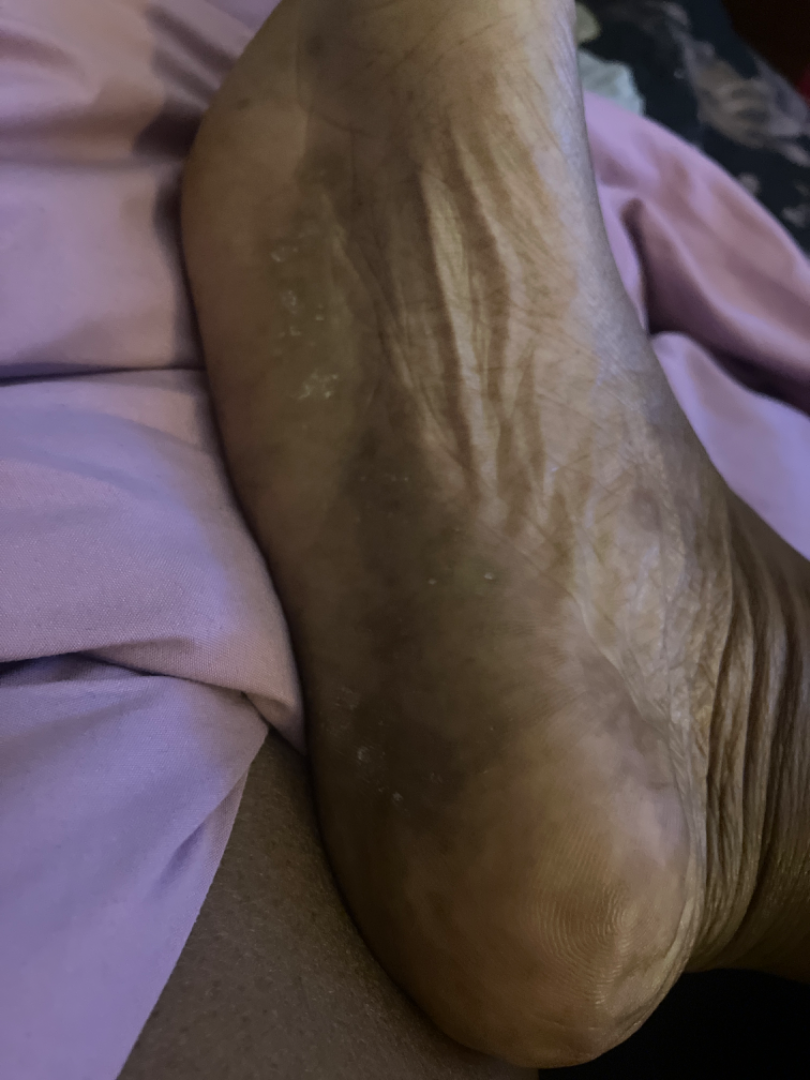differential = Psoriasis (most likely); Keratoderma (considered); Tinea (unlikely); Eczema (unlikely).